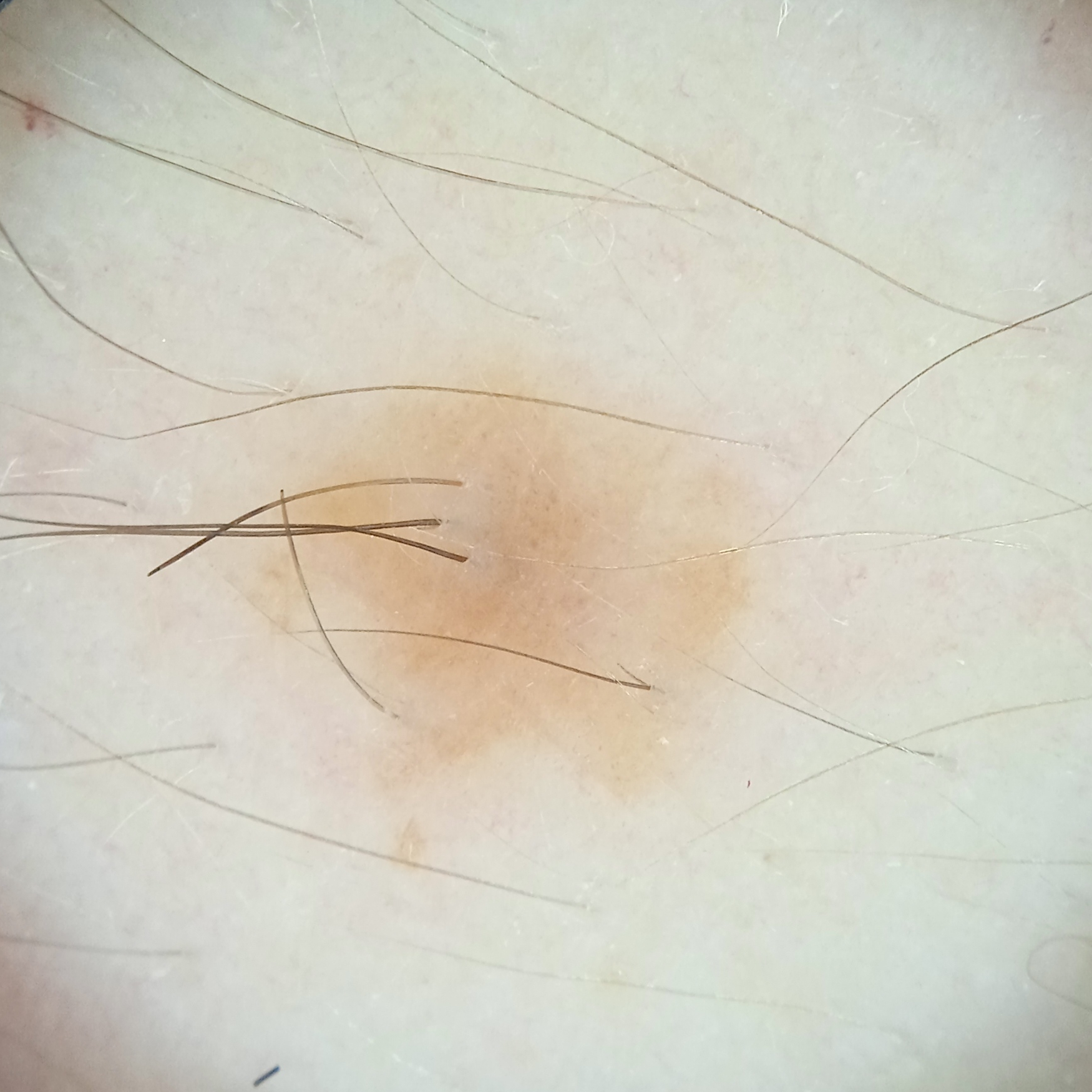image: dermoscopic image
referral: research study (no referral diagnosis)
patient: female, 35 years old
nevus count: a moderate number of melanocytic nevi
location: an arm
diameter: 5.8 mm
diagnostic label: melanocytic nevus (dermatologist consensus)